A dermoscopy image of a single skin lesion: 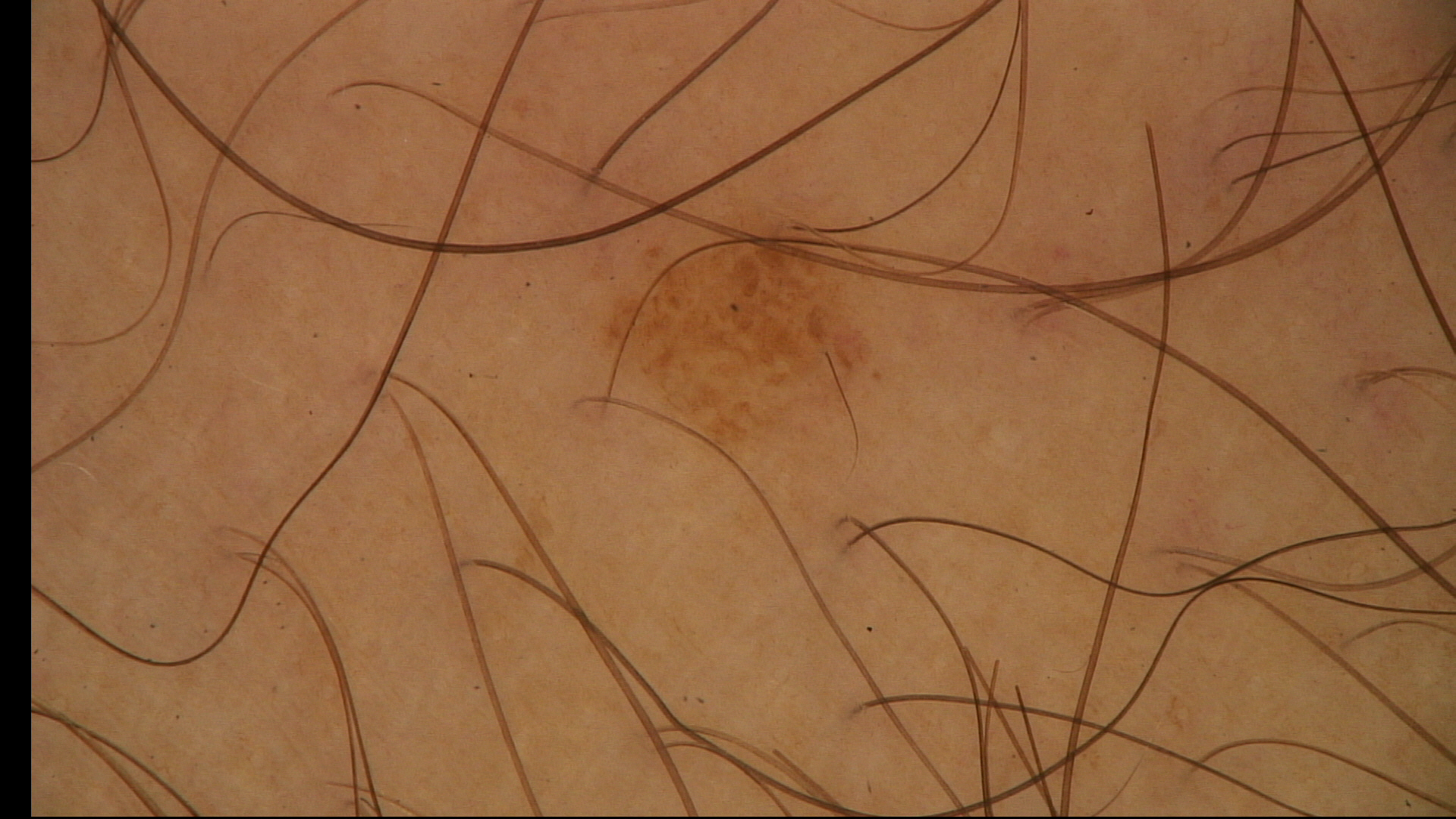Q: What is the diagnosis?
A: compound nevus (expert consensus)